A dermoscopic photograph of a skin lesion:
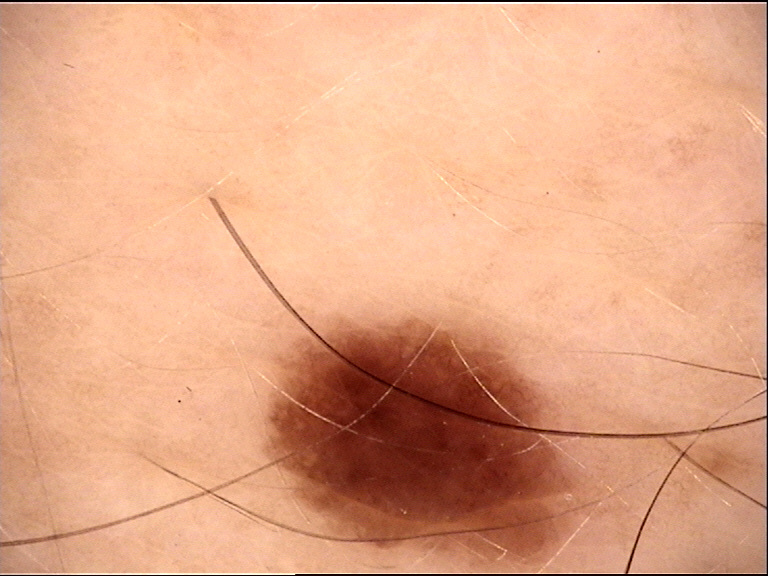Labeled as a dysplastic junctional nevus.